By history, prior malignancy (patient or family) · recorded as Fitzpatrick skin type I · a female subject in their mid-80s:
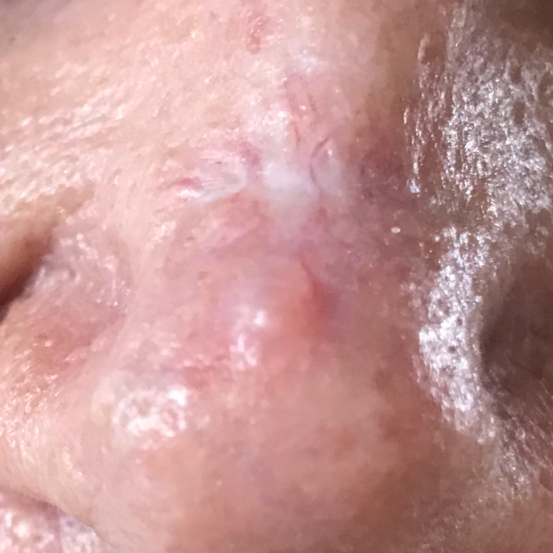body site: the nose, pathology: basal cell carcinoma (biopsy-proven).